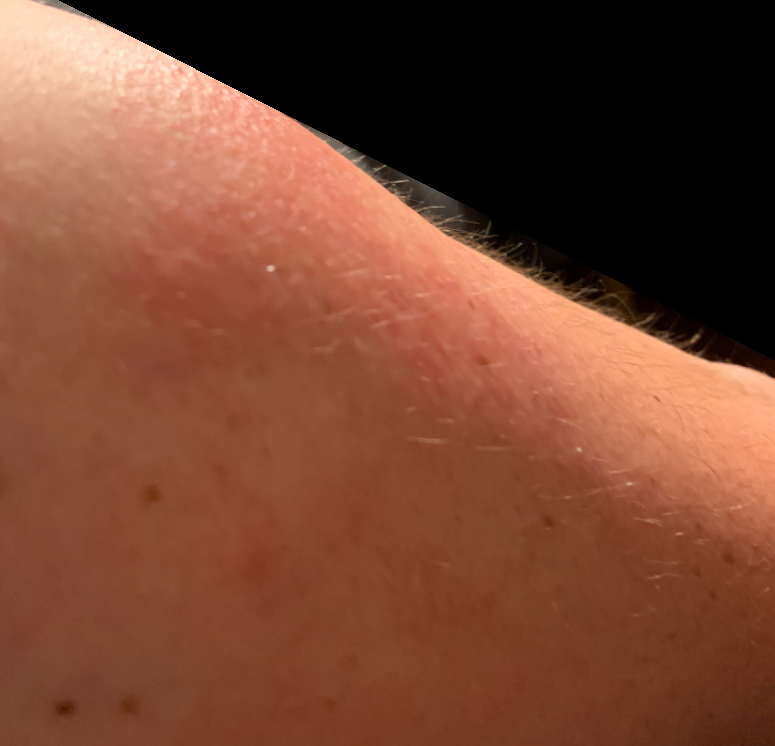The reviewer was unable to grade this case for skin condition.
The affected area is the arm.
An image taken at an angle.